A dermoscopic close-up of a skin lesion.
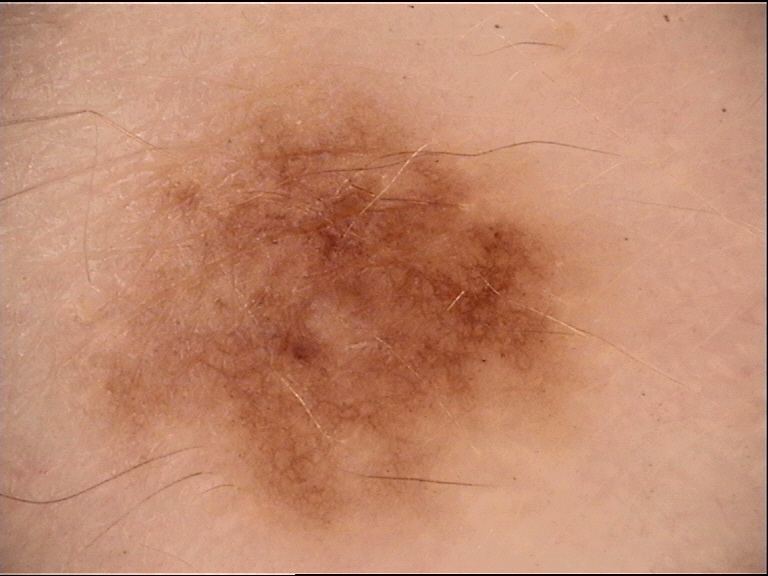Labeled as a benign lesion — a dysplastic junctional nevus.